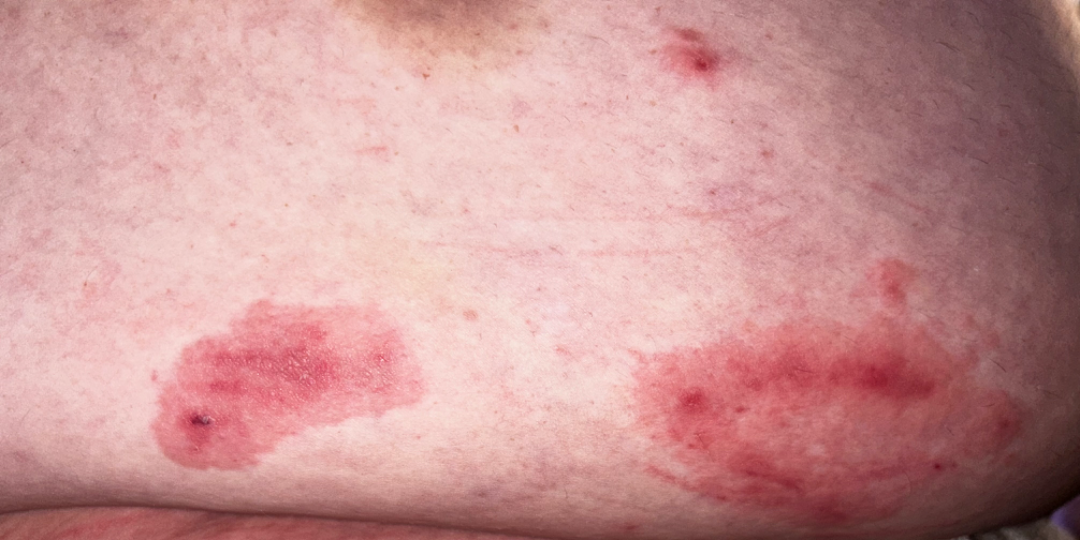assessment = indeterminate from the photograph